A dermatoscopic image of a skin lesion:
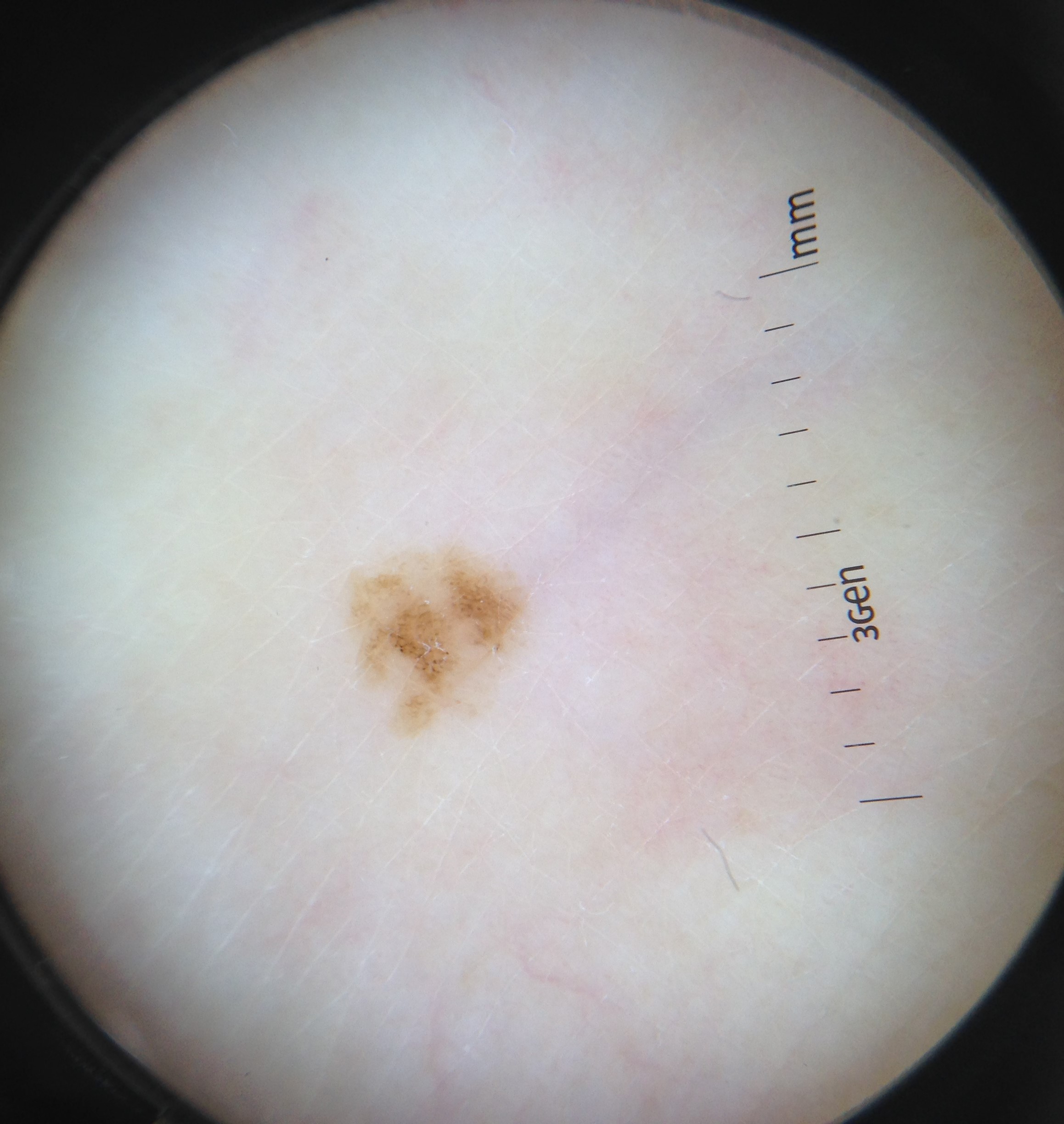diagnostic label: dysplastic junctional nevus (expert consensus)